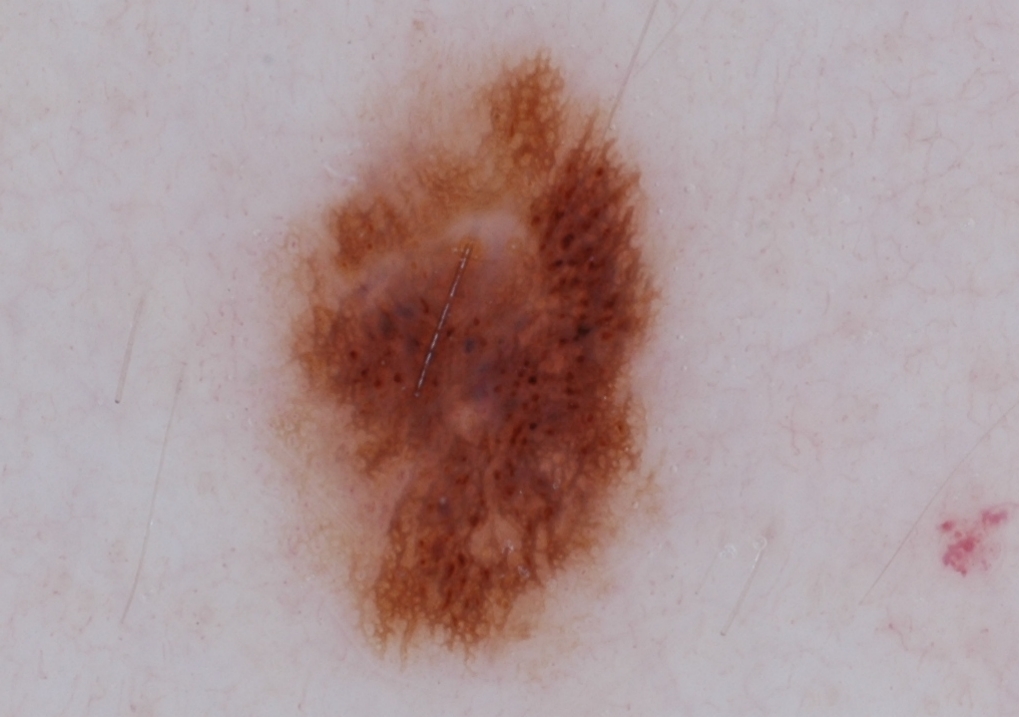A dermoscopic view of a skin lesion. Dermoscopic assessment notes pigment network, globules, and streaks; no milia-like cysts or negative network. In (x1, y1, x2, y2) order, the visible lesion spans bbox(272, 48, 666, 658). The clinical diagnosis was a melanocytic nevus.